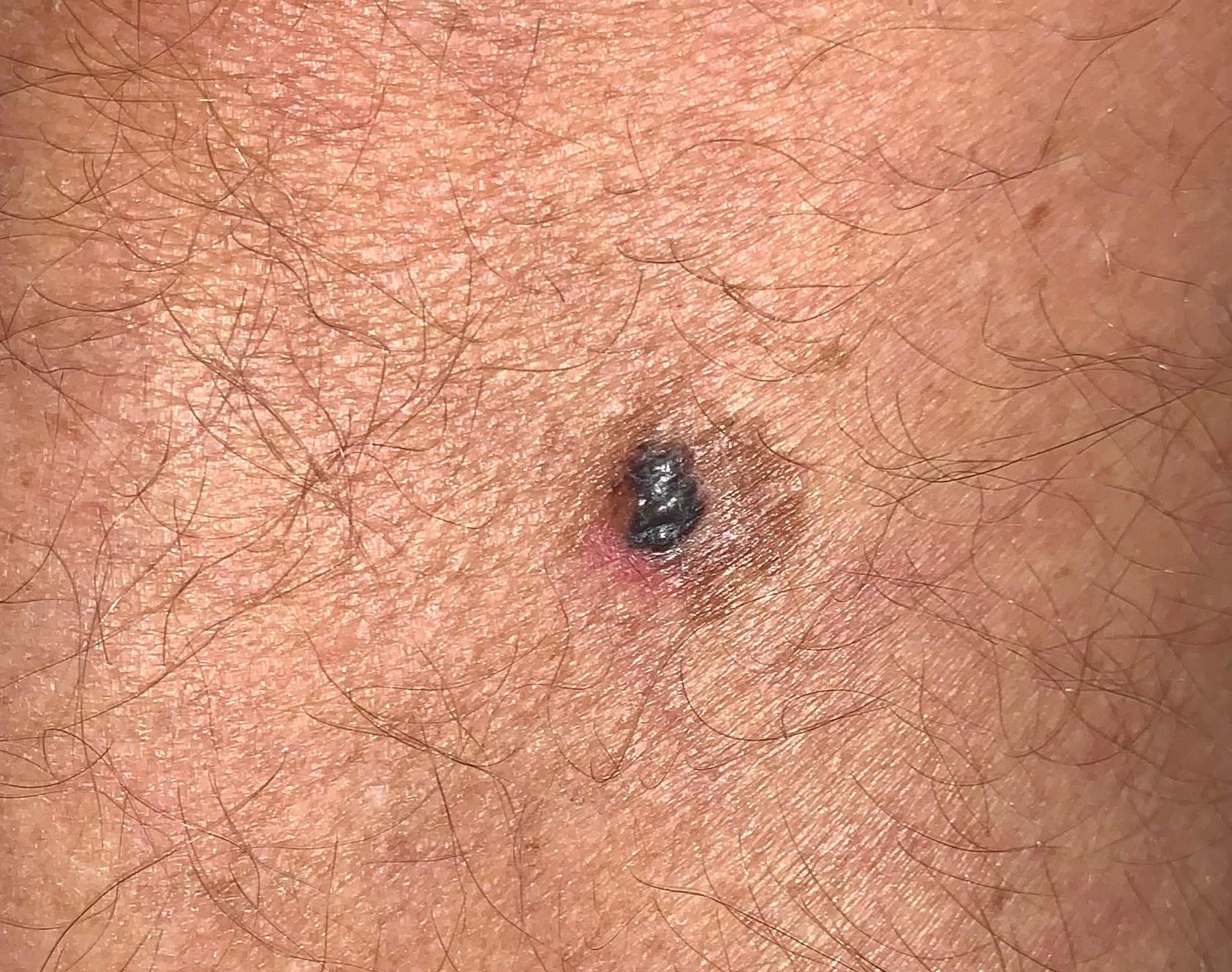Case:
• skin type · II
• patient · male, aged around 60
• imaging · clinical photo (overview)
• site · a lower extremity
• diagnosis · Melanoma (biopsy-proven)